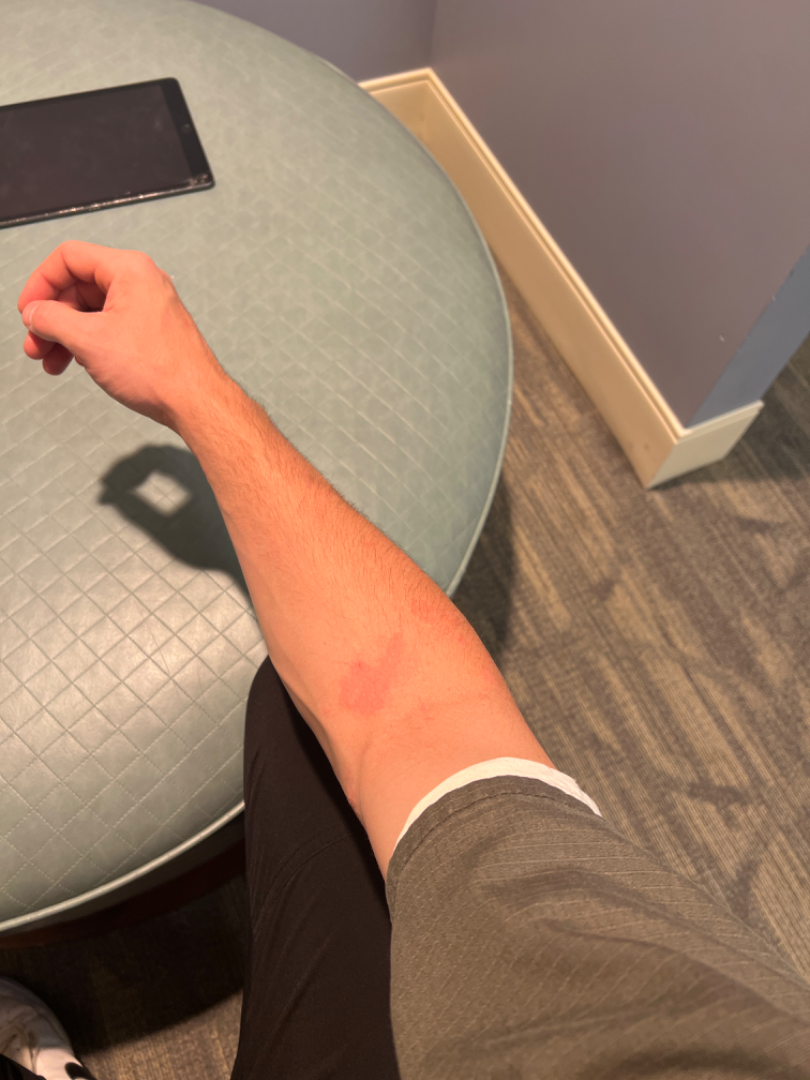location = arm; contributor = male, age 18–29; view = at a distance; diagnostic considerations = Eczema (most likely).